This is a close-up image. The patient is female. The affected area is the head or neck, arm and front of the torso: 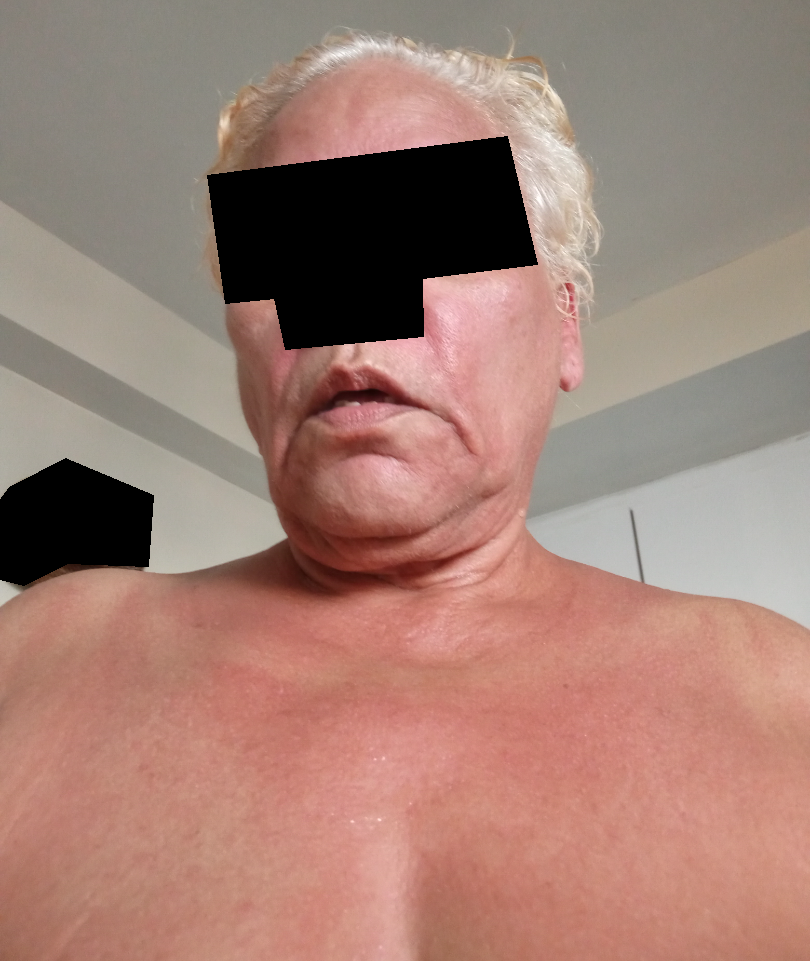The reviewing dermatologists' impression was: the differential, in no particular order, includes Photodermatitis and Vitiligo.